A skin lesion imaged with a dermatoscope: 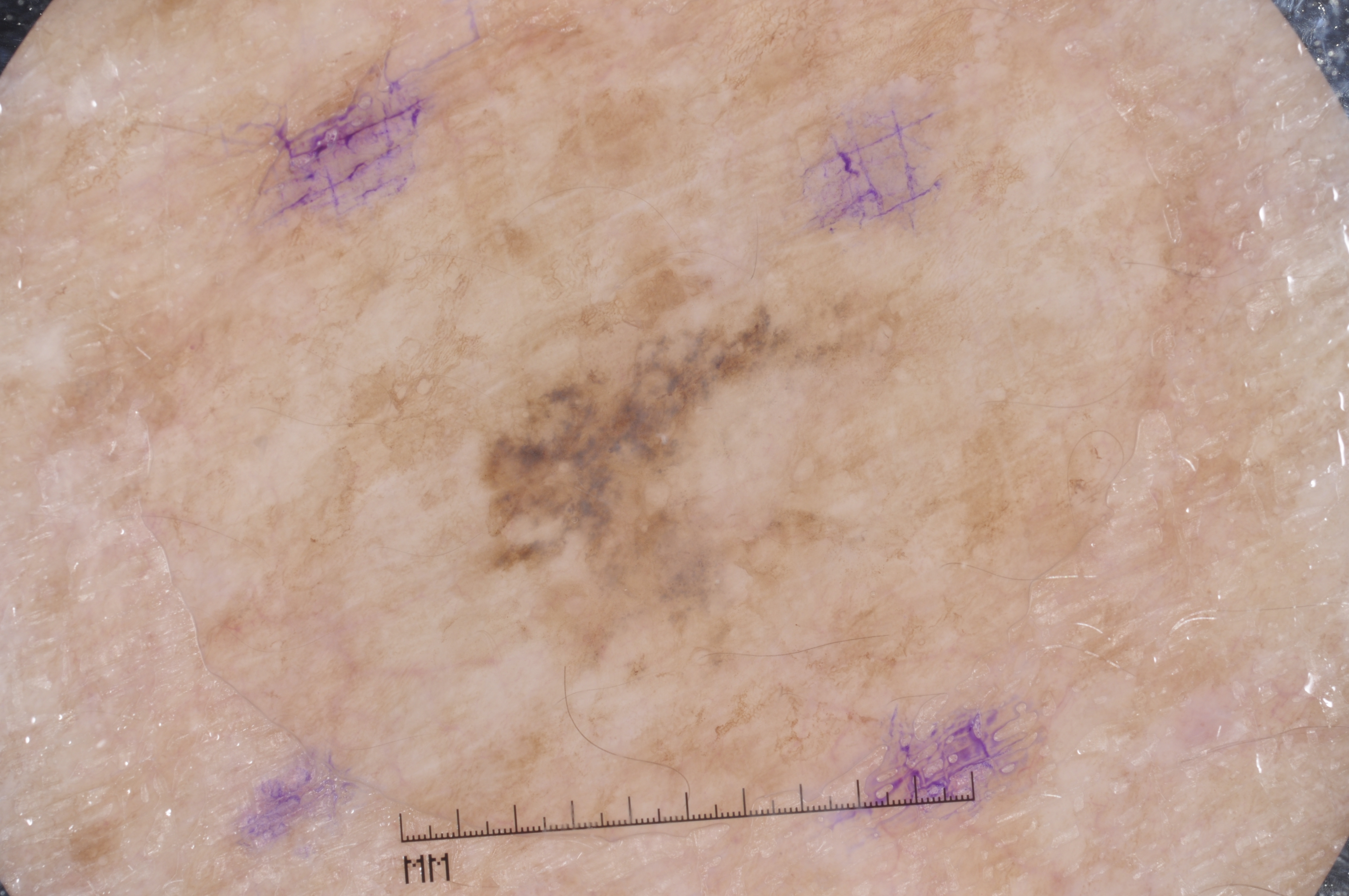As (left, top, right, bottom), the lesion spans 472, 281, 910, 666.
Dermoscopically, the lesion shows no pigment network, negative network, streaks, or milia-like cysts.
Histopathological examination showed a melanoma.